This is a close-up image; the contributor notes the lesion is rough or flaky and raised or bumpy; the lesion involves the back of the hand; the patient considered this a nail problem; the subject is 18–29, male; the contributor notes pain, enlargement, bothersome appearance, darkening and bleeding; the condition has been present for three to twelve months: 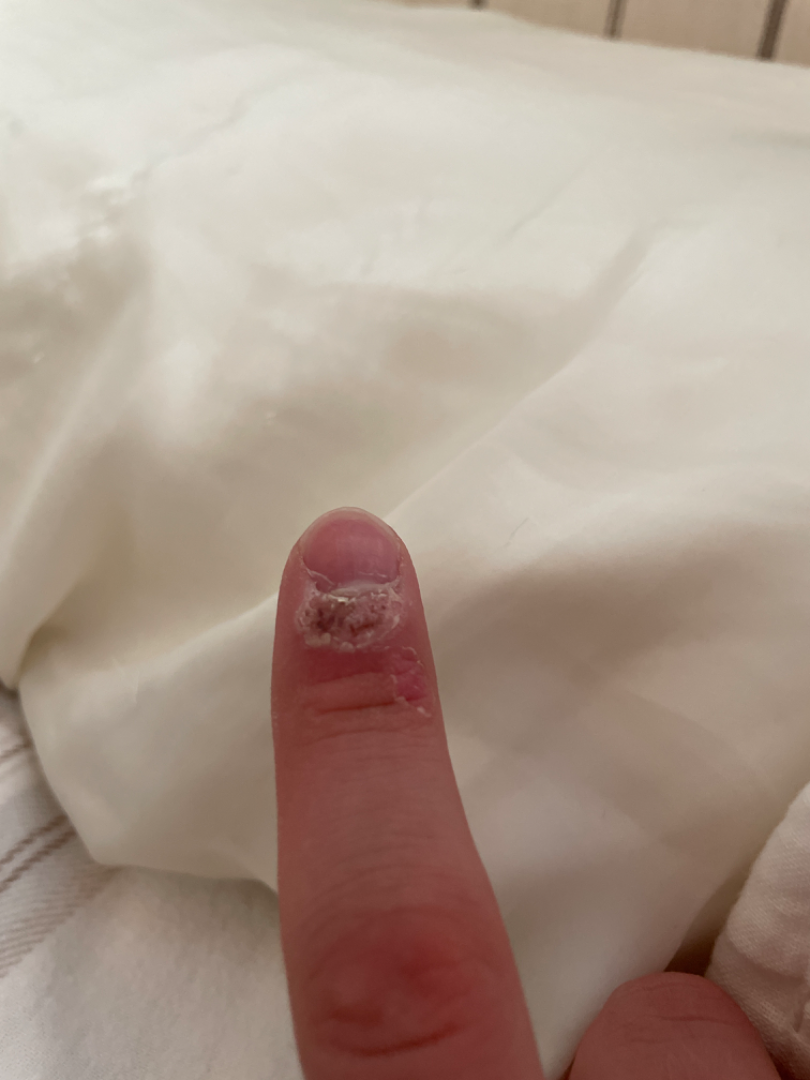Most consistent with Verruca vulgaris; also consider Clavus; also raised was SCC/SCCIS.